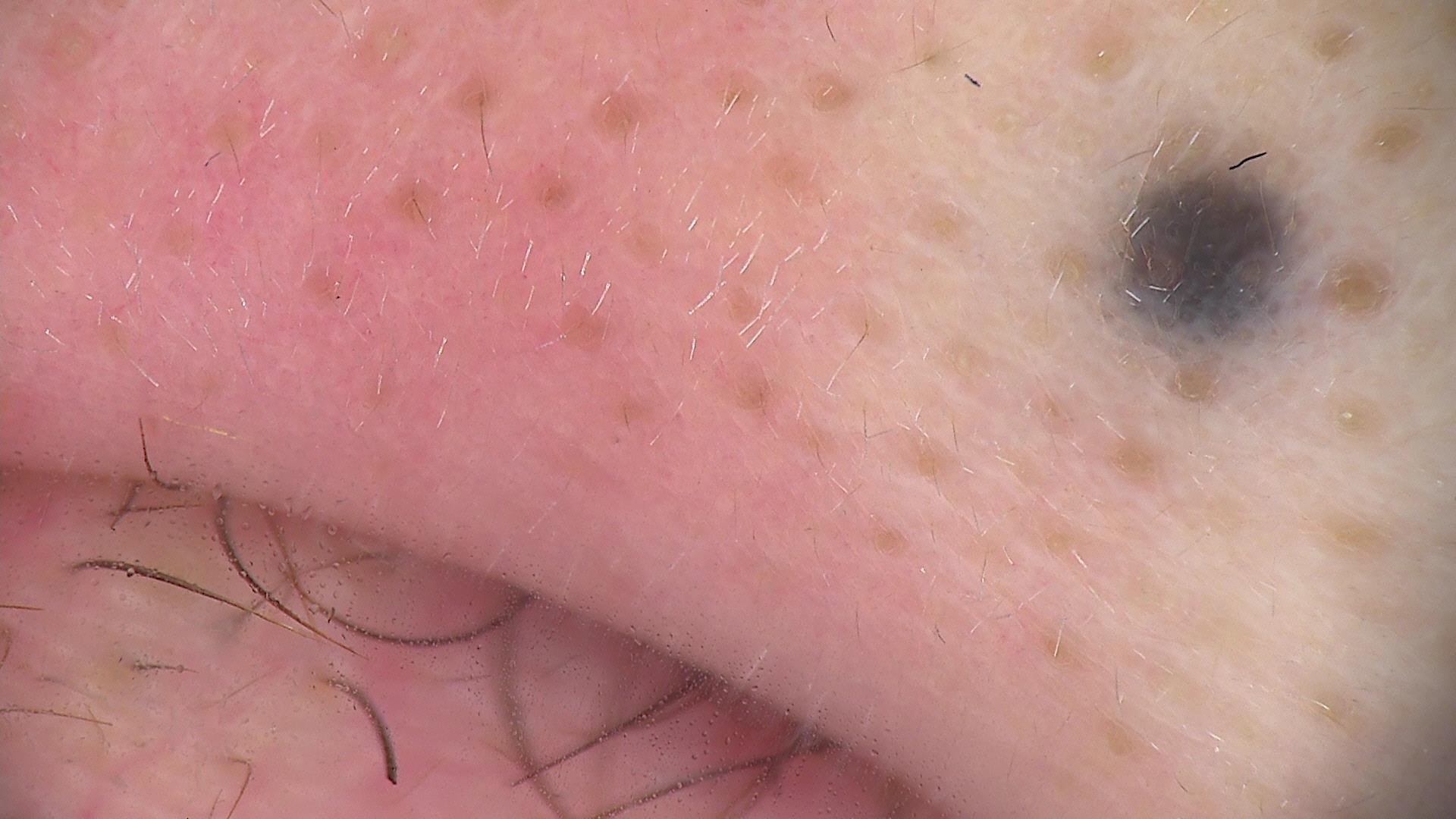label: blue nevus (expert consensus).